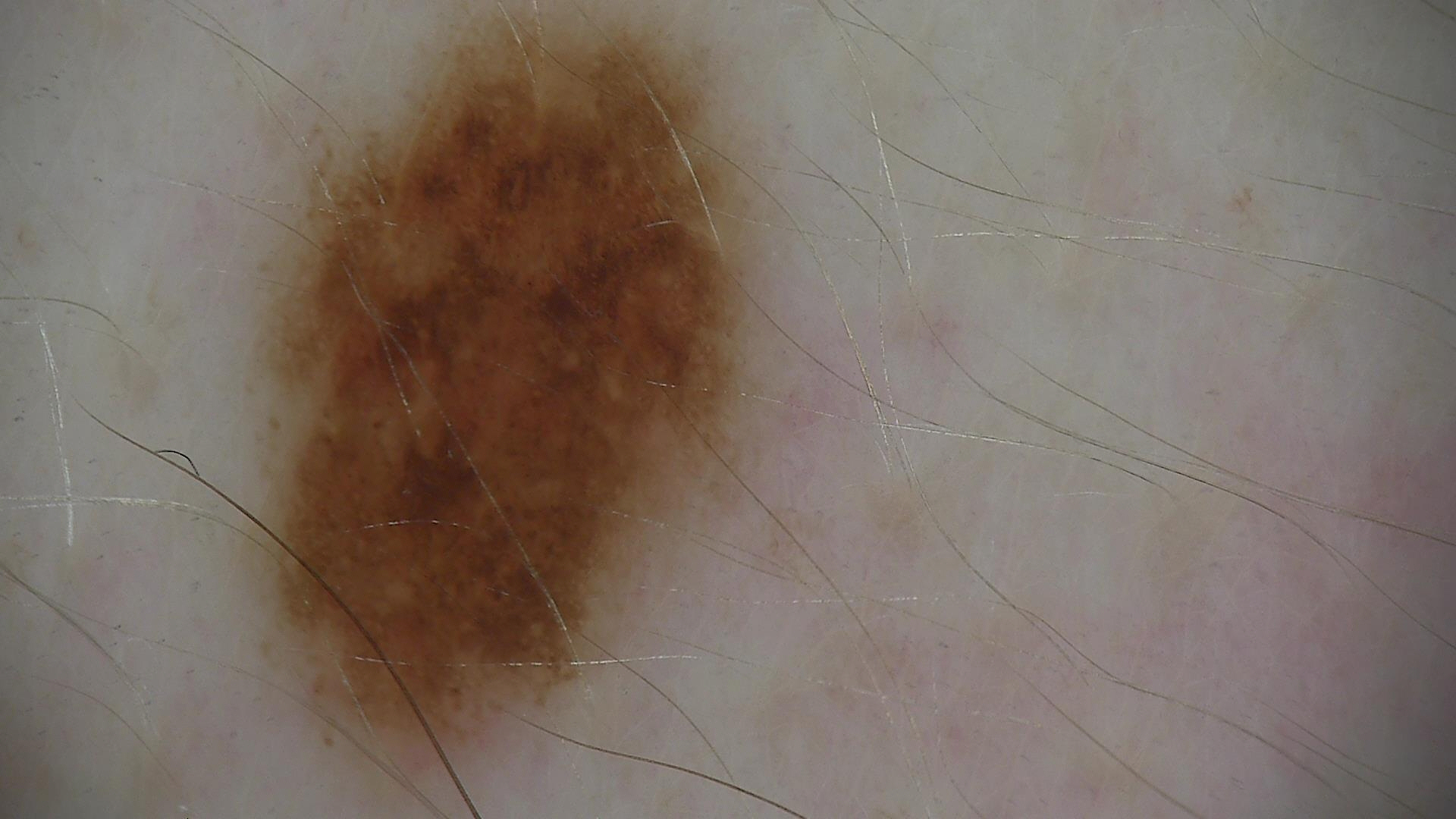Case: A dermoscopy image of a single skin lesion. Impression: Classified as a dysplastic junctional nevus.